Dermoscopy of a skin lesion.
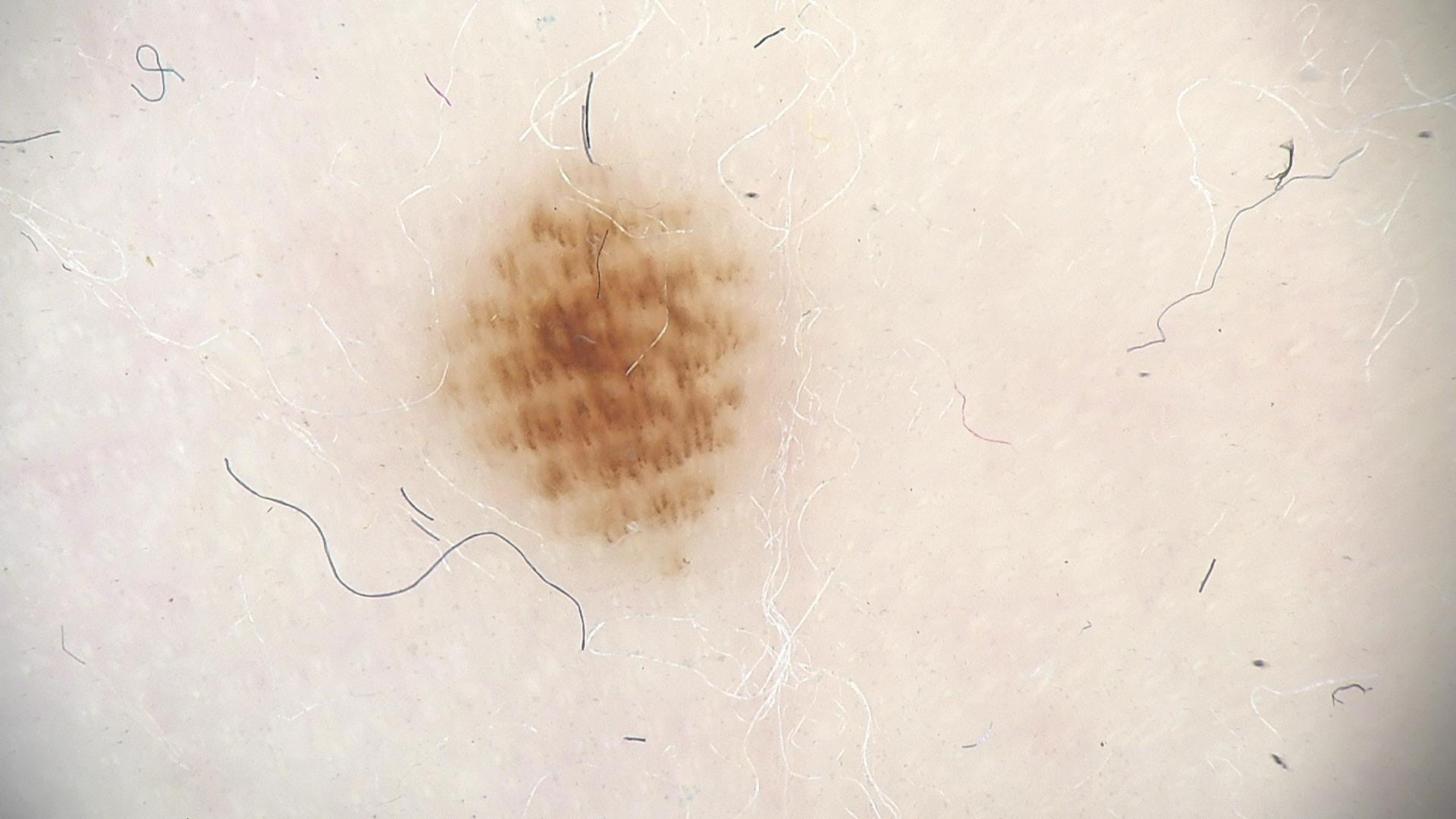class = acral dysplastic junctional nevus (expert consensus).